A female patient 60 years old. The patient describes having few moles overall. Imaged for a research study, with no referral diagnosis recorded. On a questionnaire the patient reported a personal history of cancer and a personal history of skin cancer. The patient says their skin tans without first burning. A dermoscopic image of a skin lesion.
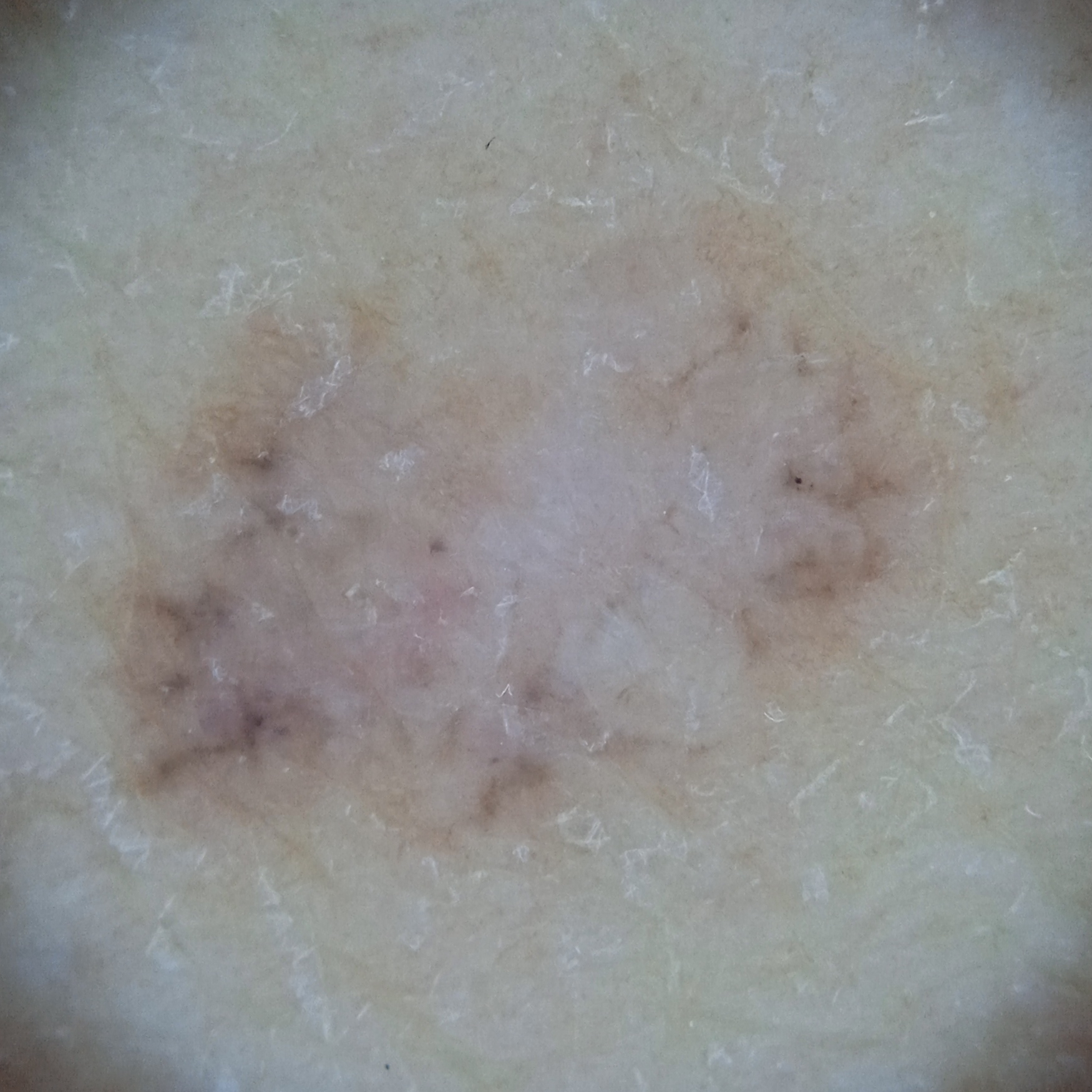Case:
- anatomic site: the back
- diameter: 10.4 mm
- diagnosis: basal cell carcinoma (dermatologist consensus)